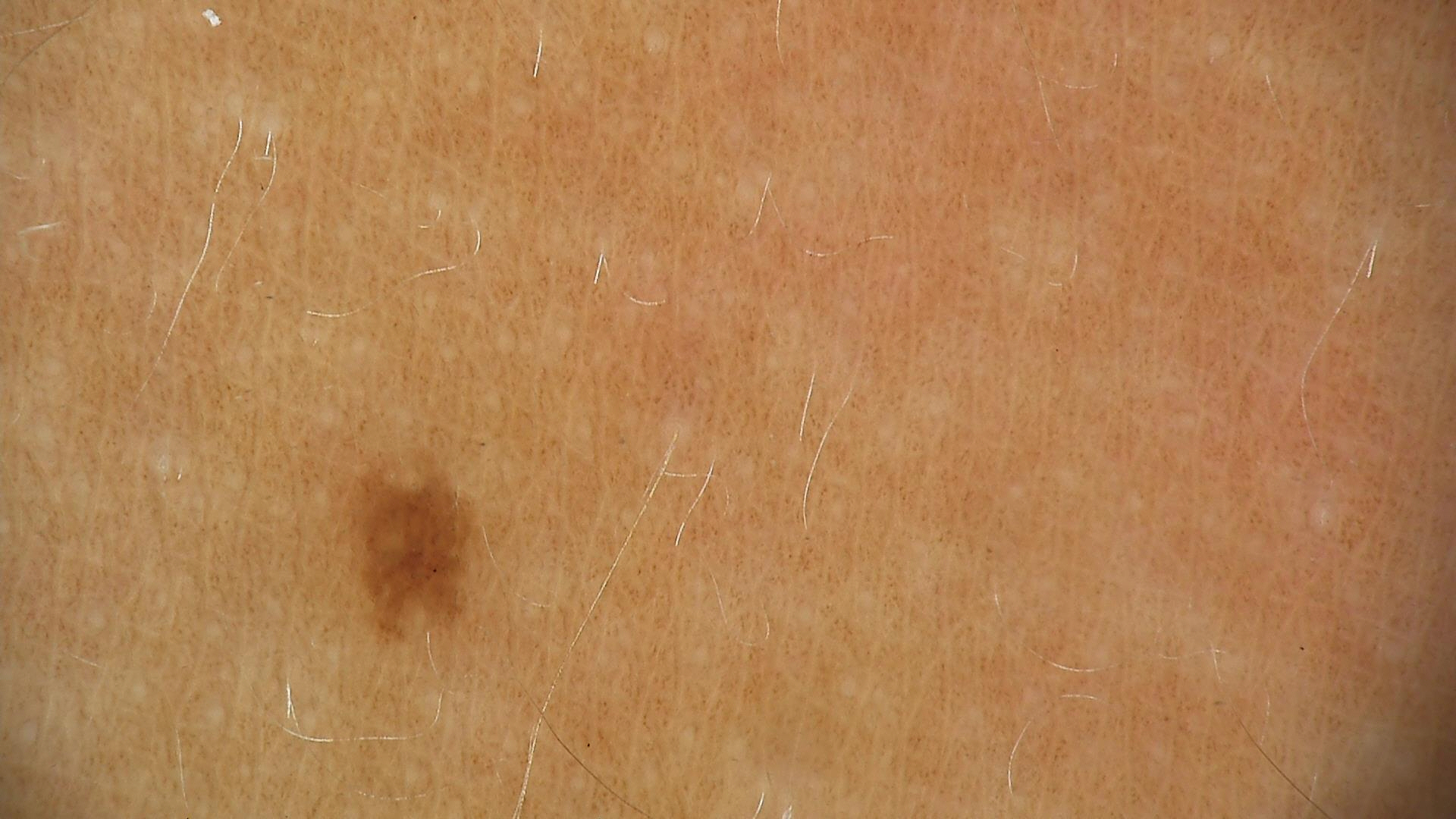image=dermoscopy
diagnosis=dysplastic junctional nevus (expert consensus)